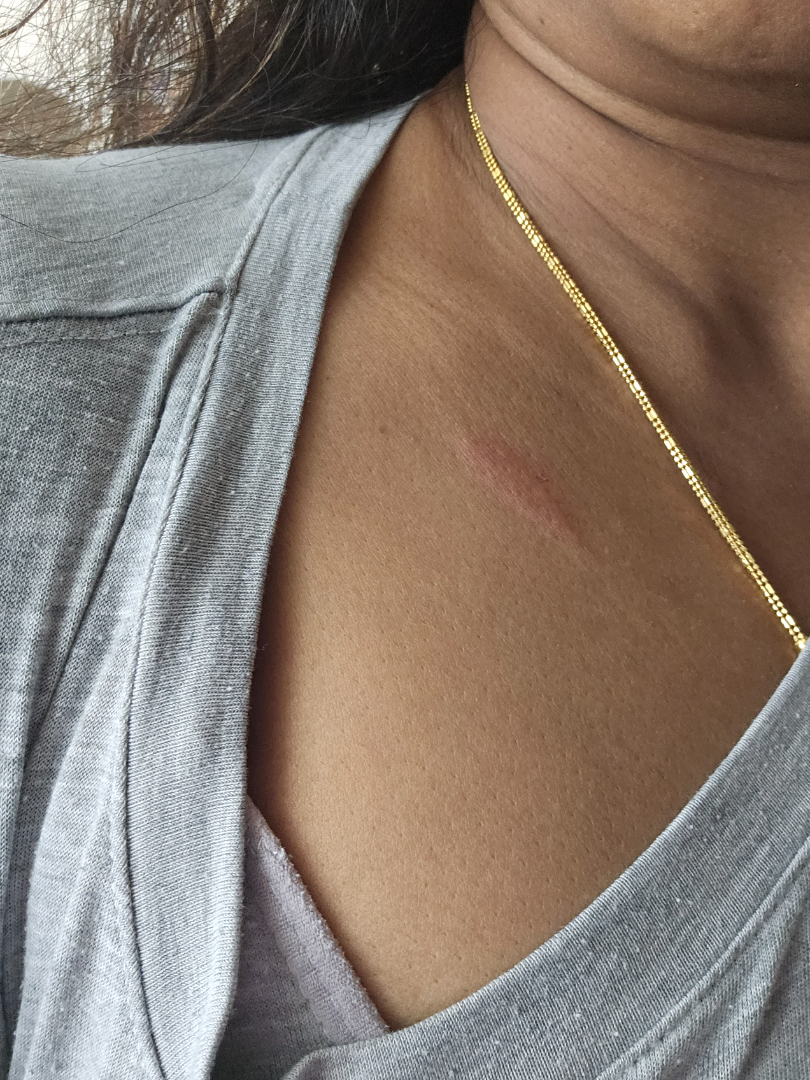assessment = unable to determine | view = close-up.